A female patient aged 32; a smartphone photograph of a skin lesion; the patient was assessed as Fitzpatrick phototype II:
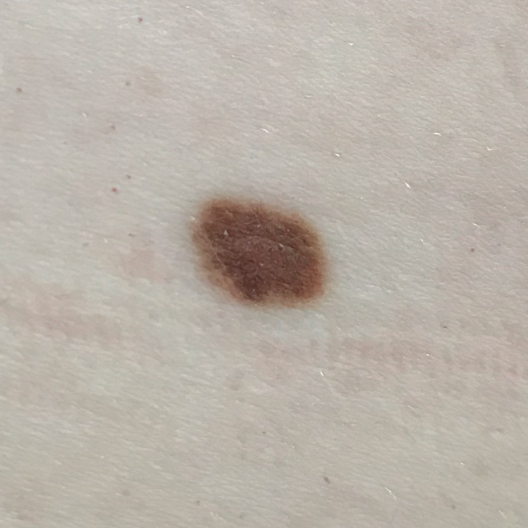The lesion is located on a thigh.
The lesion measures 7 × 7 mm.
The patient describes that the lesion itches, has changed, and has grown, but is not elevated.
Biopsy-confirmed as a nevus.